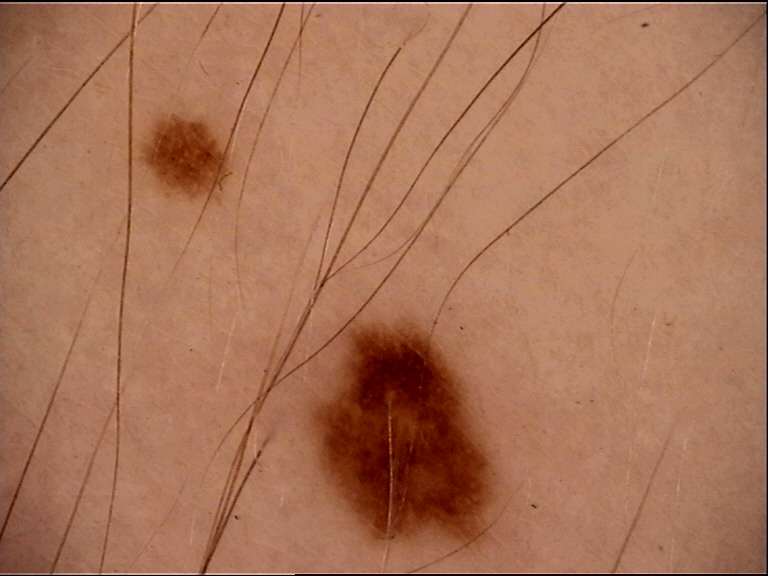A dermoscopic photograph of a skin lesion. Diagnosed as a dysplastic junctional nevus.